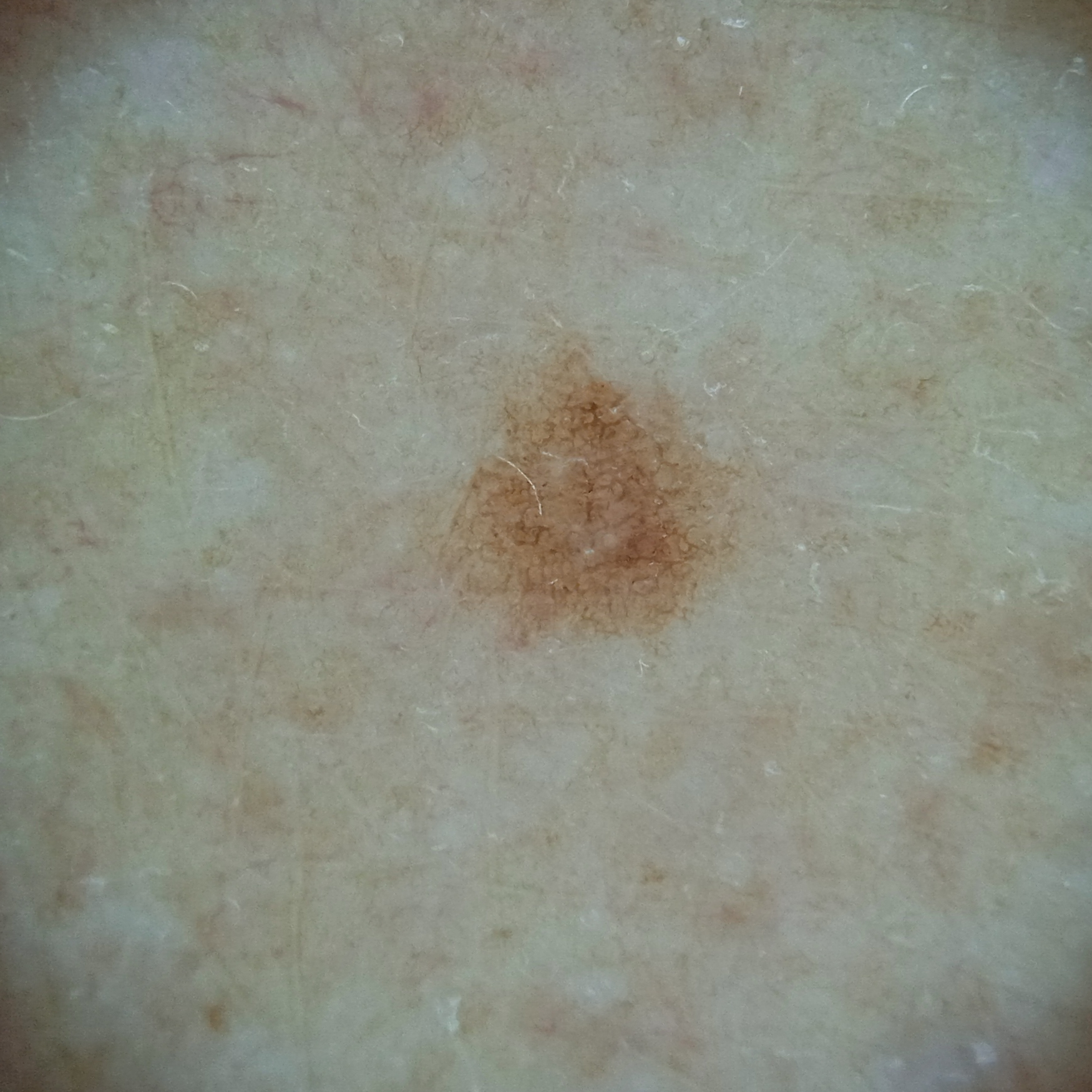referral=research study (no referral diagnosis); risk factors=a personal history of cancer, a personal history of skin cancer; nevus count=few melanocytic nevi overall; image type=dermatoscopic image; body site=an arm; assessment=melanocytic nevus (dermatologist consensus).